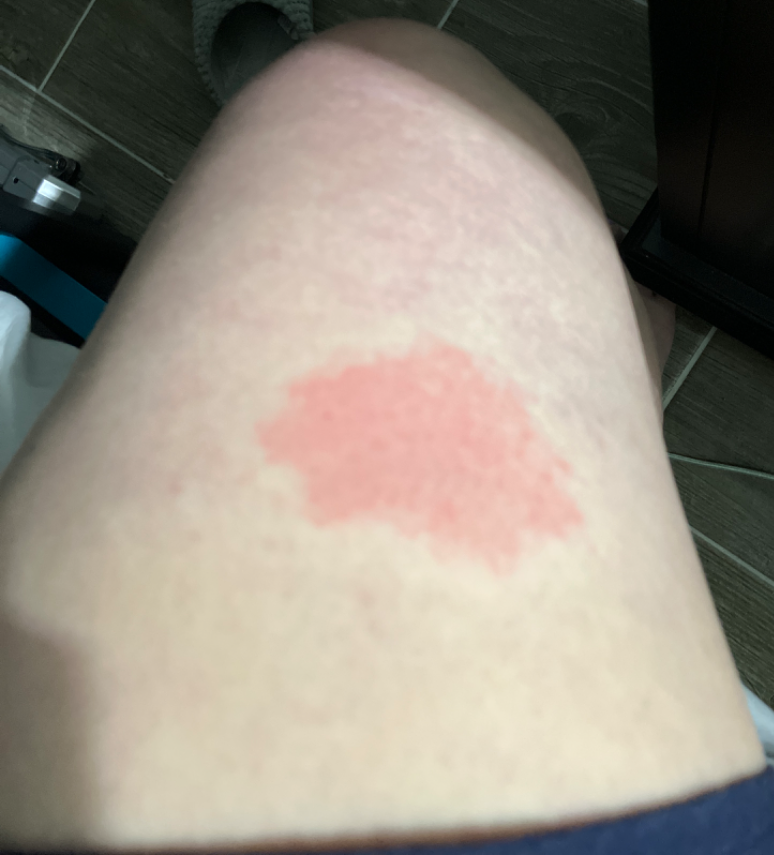Assessment: No differential diagnosis could be assigned on photographic review. Clinical context: Located on the leg. The patient considered this a rash. Close-up view. The patient notes the lesion is raised or bumpy. The condition has been present for less than one week. The patient notes bothersome appearance.